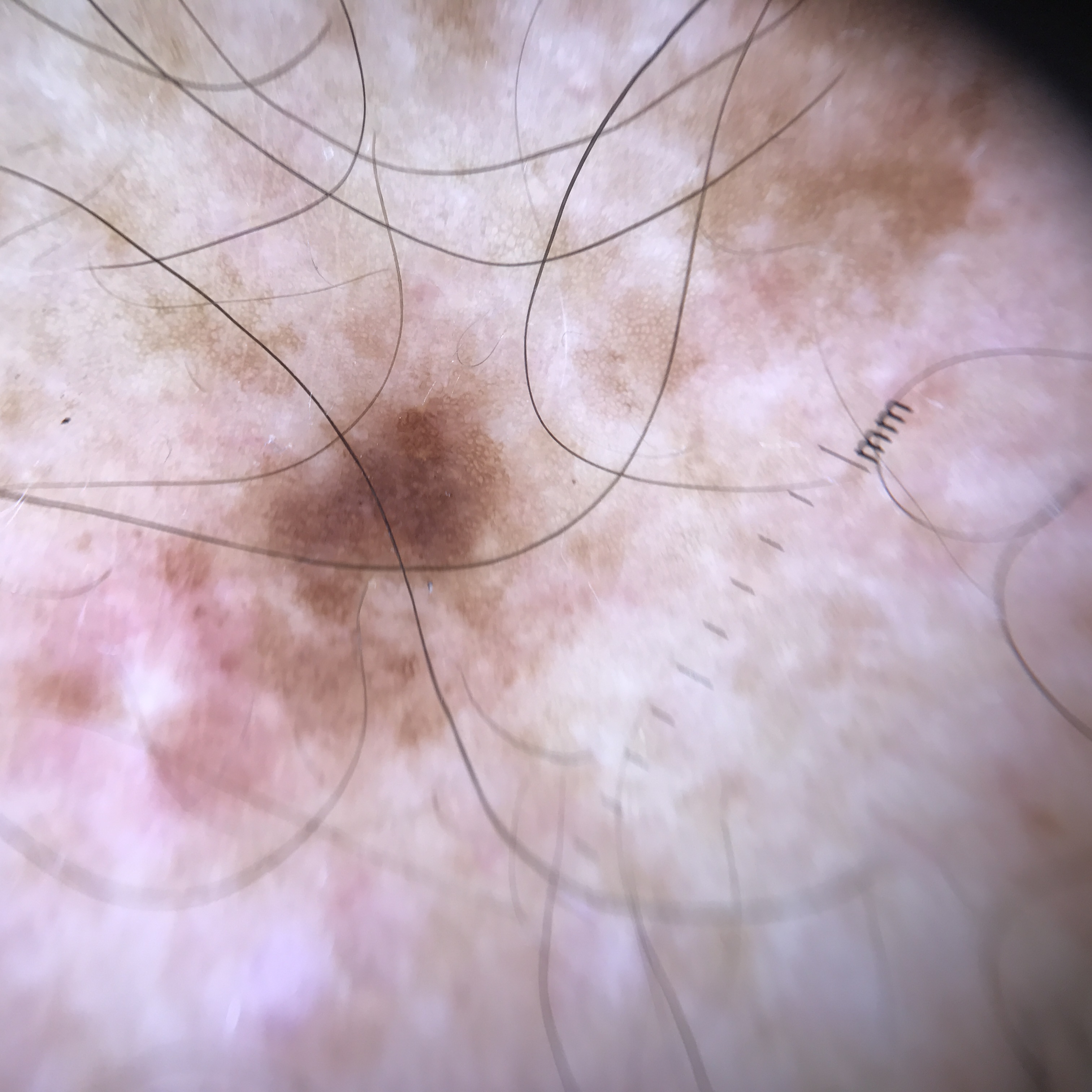Impression: The diagnostic label was a solar lentigo.